The subject is a male aged approximately 80, a dermoscopy image of a single skin lesion — 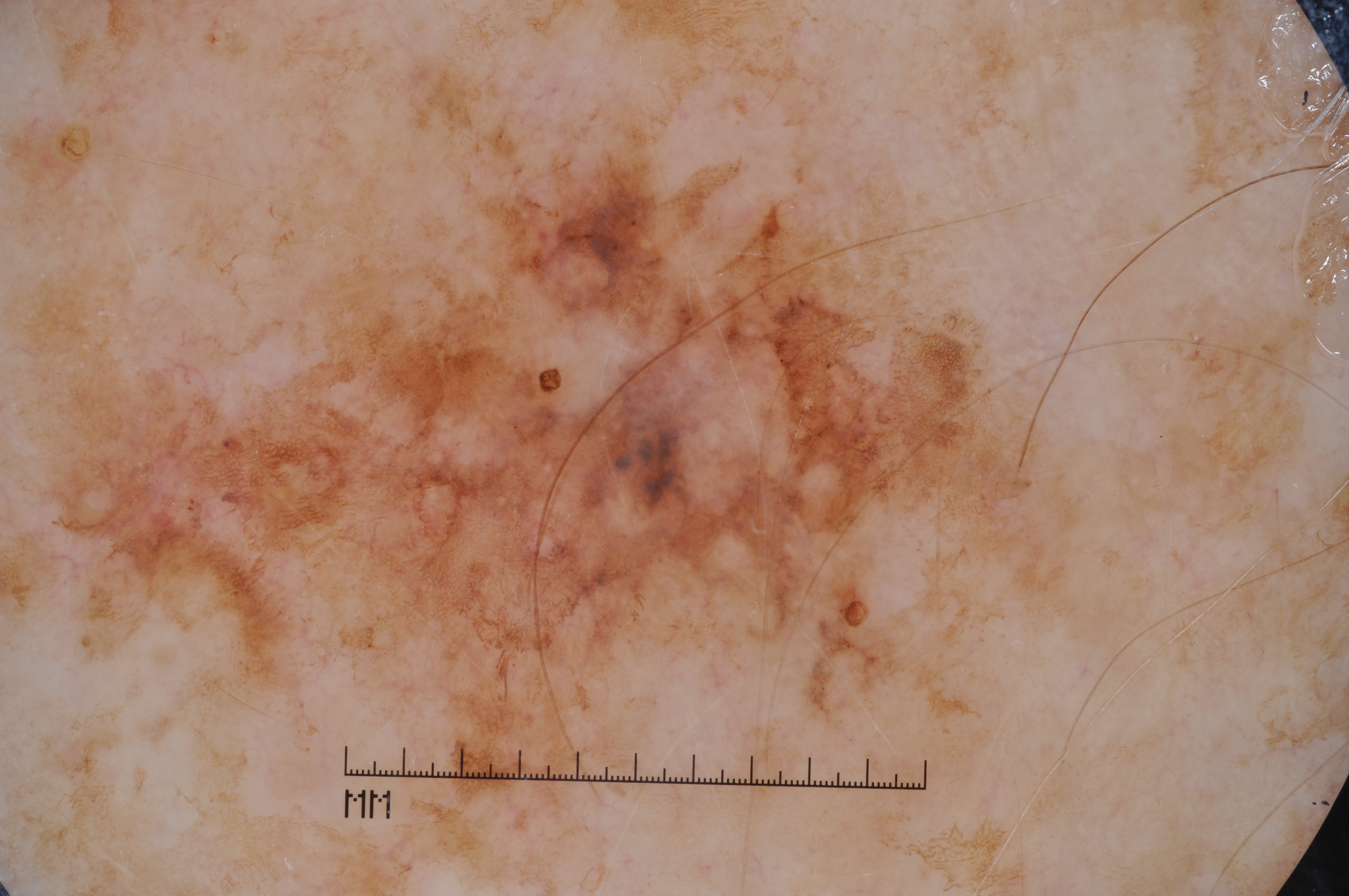extent = large; dermoscopic features = milia-like cysts and pigment network; bounding box = [53, 126, 1064, 791]; diagnostic label = a melanoma.